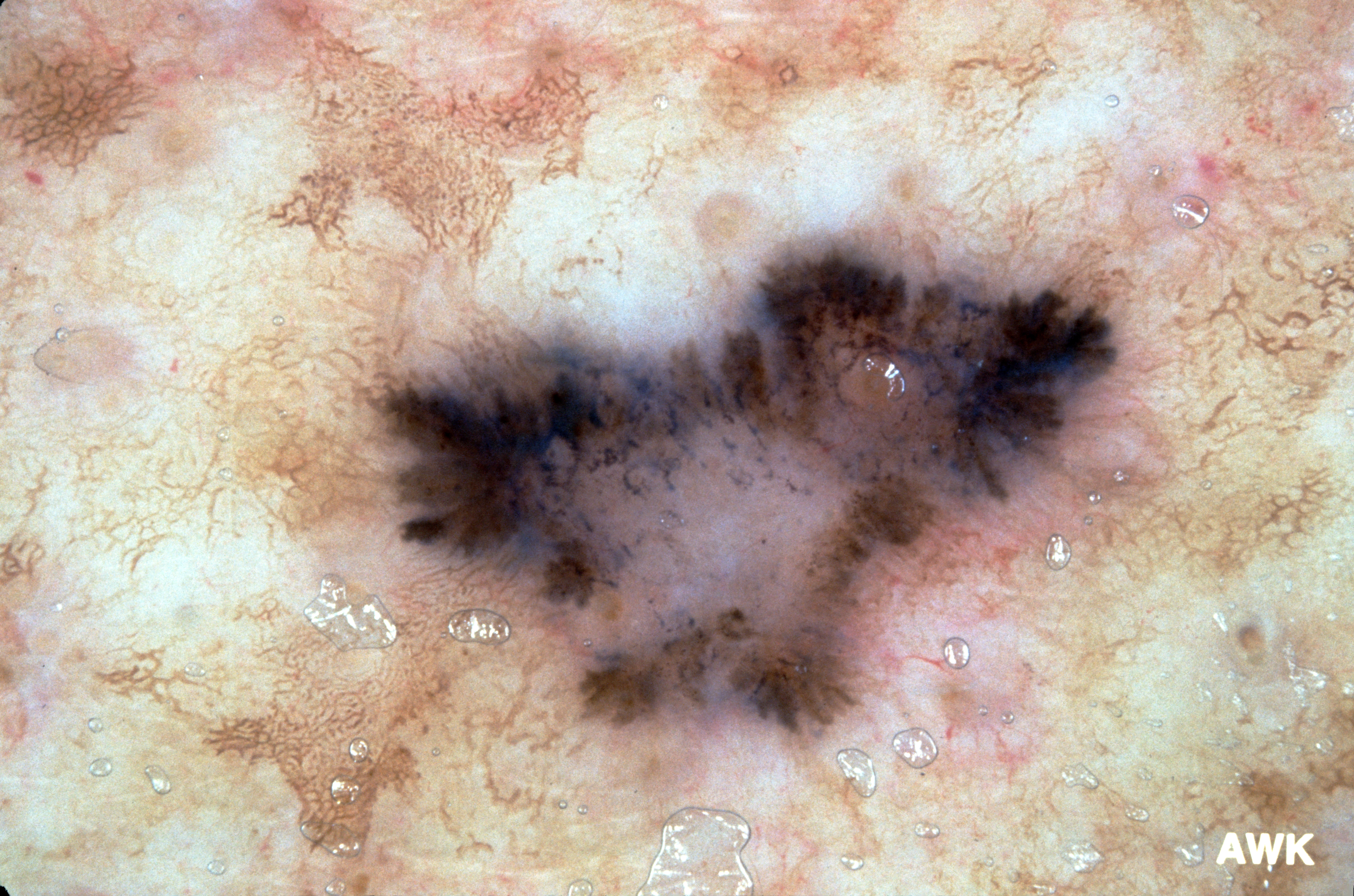image = dermoscopy | subject = female, aged 33 to 37 | lesion location = [357, 174, 1178, 771] | lesion extent = ~28% of the field | dermoscopic findings = pigment network and streaks; absent: milia-like cysts and negative network | assessment = a melanoma, a malignancy.